This image was taken at an angle. Located on the arm. Female contributor, age 18–29: 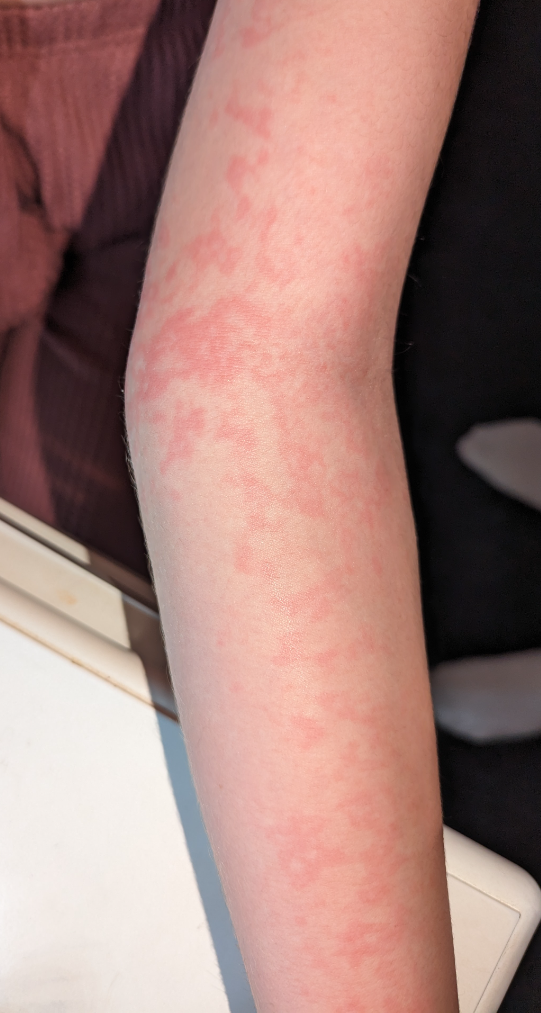Review:
The condition could not be reliably identified from the image.
Patient information:
The patient reports the condition has been present for less than one week. The patient reports the lesion is flat. The lesion is associated with bothersome appearance.